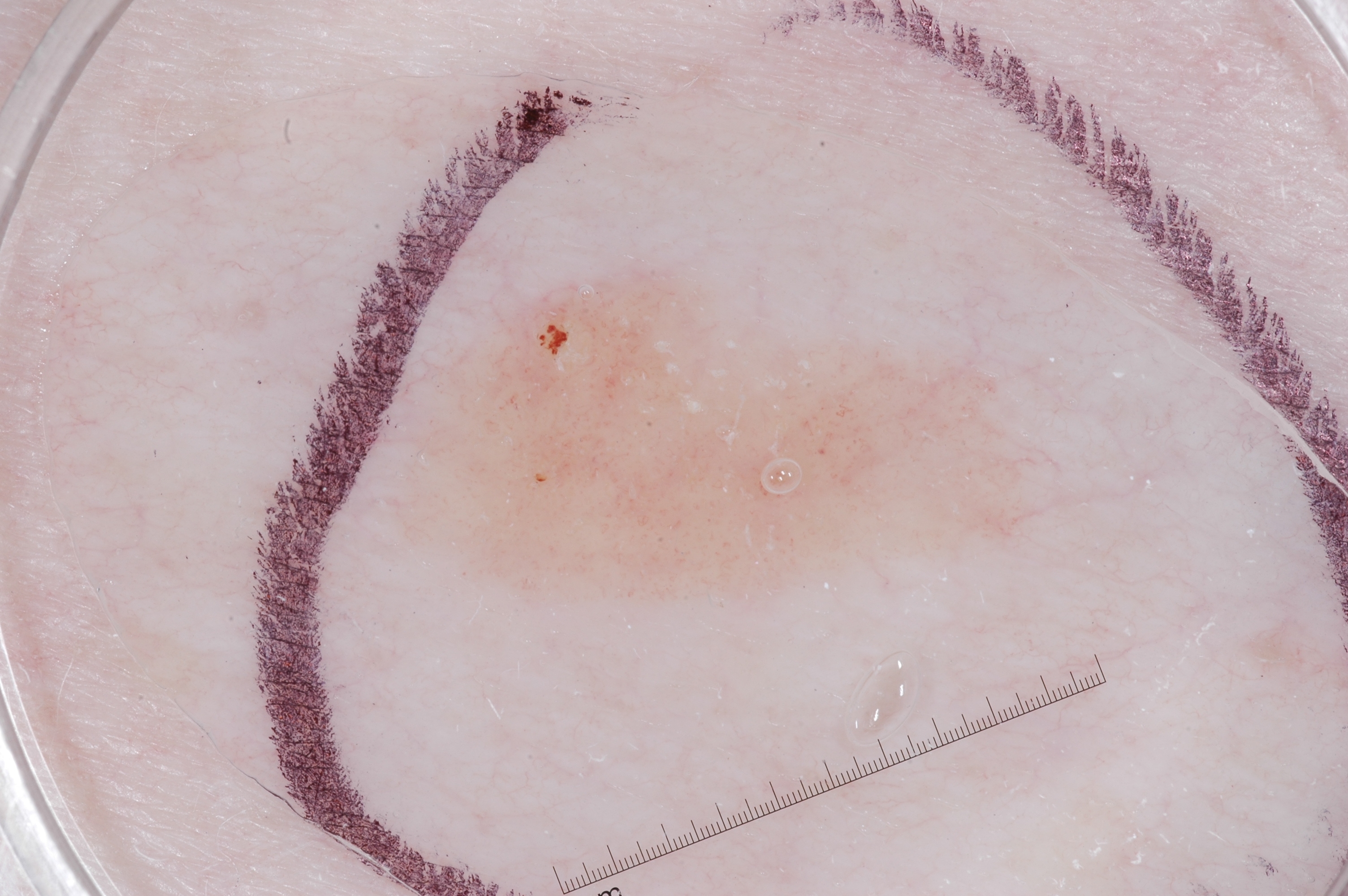{"image": {"modality": "dermoscopy"}, "lesion_location": {"bbox_xyxy": [384, 275, 1070, 614]}, "diagnosis": {"name": "seborrheic keratosis", "malignancy": "benign", "lineage": "keratinocytic", "provenance": "clinical"}}